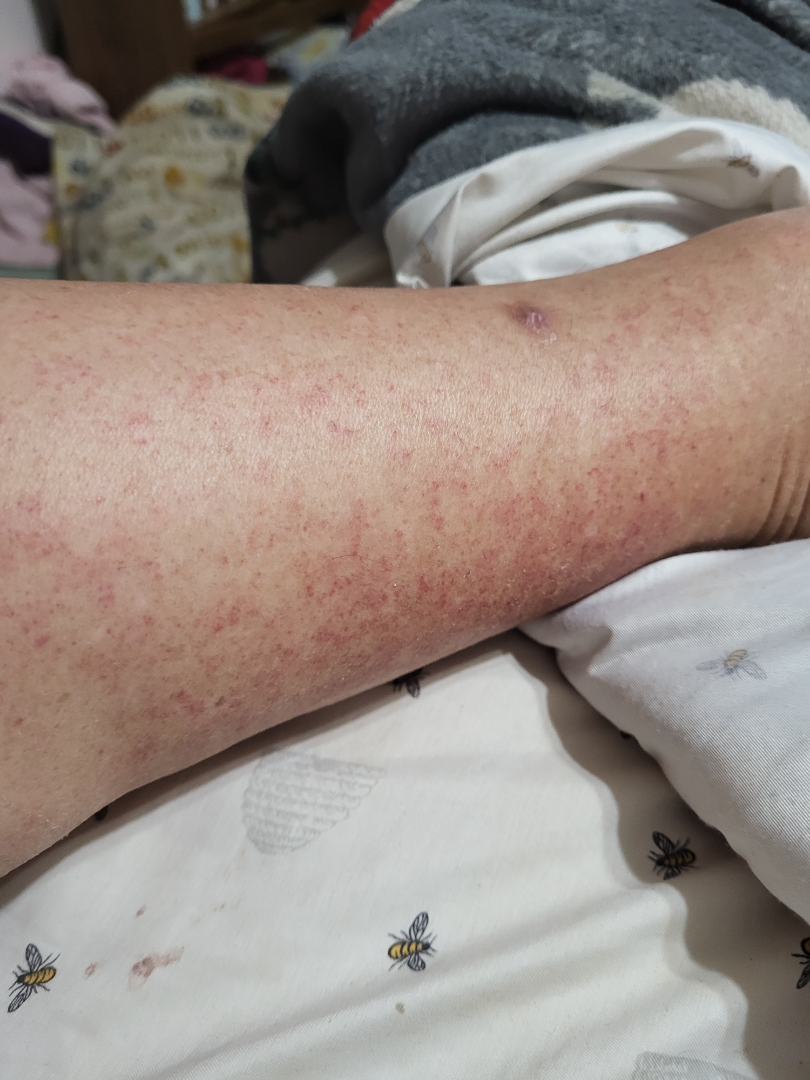Self-categorized by the patient as a rash. An image taken at an angle. Present for less than one week. The leg is involved. The contributor notes the lesion is flat. The patient is a female aged 60–69. Skin tone: Fitzpatrick phototype II; lay reviewers estimated Monk Skin Tone 3 or 4 (two reviewer pools). The lesion is associated with itching, burning and bleeding. On teledermatology review: Stasis Dermatitis (0.50); Allergic Contact Dermatitis (0.29); Pigmented purpuric eruption (0.21).